The photograph is a close-up of the affected area — 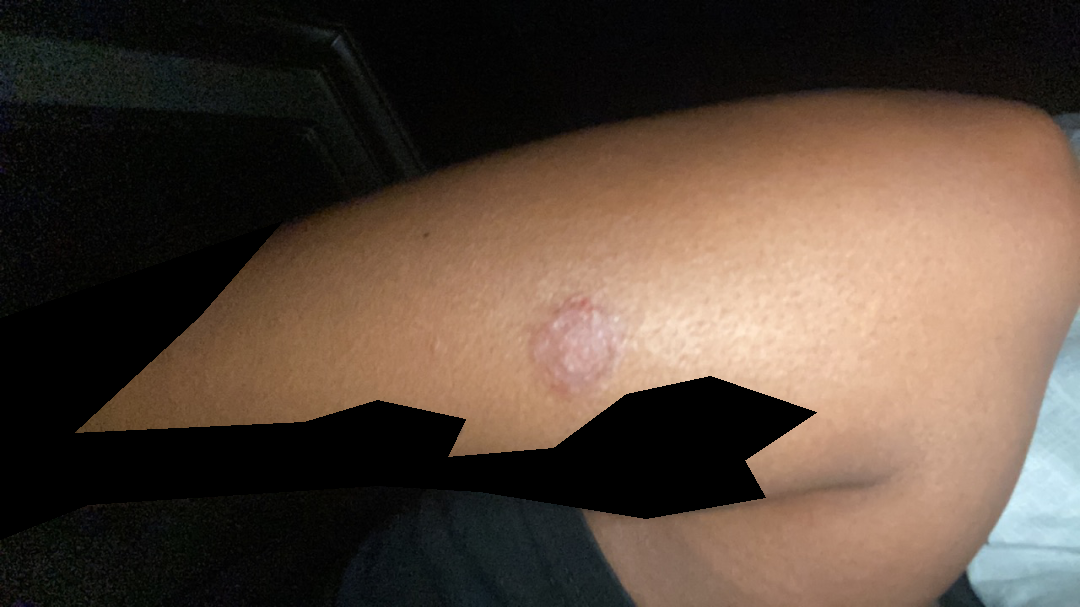Review: The image was not sufficient for the reviewer to characterize the skin condition.